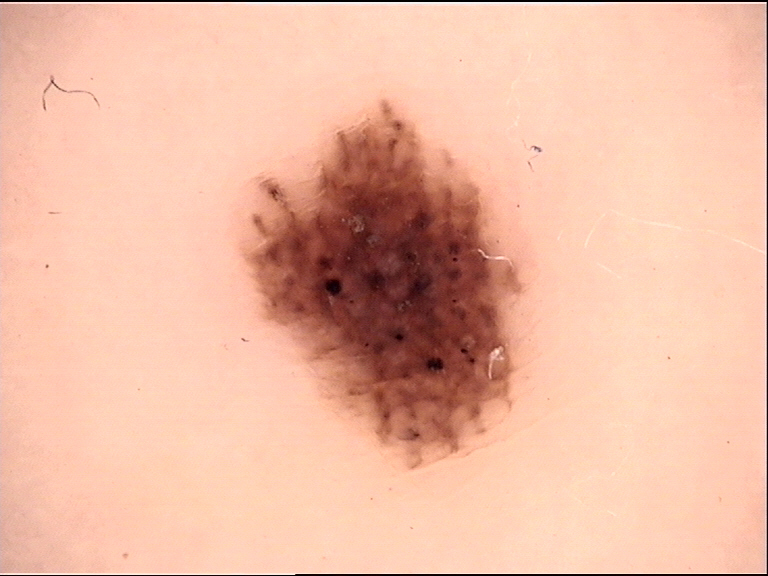The diagnostic label was a benign lesion — an acral dysplastic junctional nevus.